Present for about one day, this image was taken at a distance, the patient also reports fatigue, located on the arm — 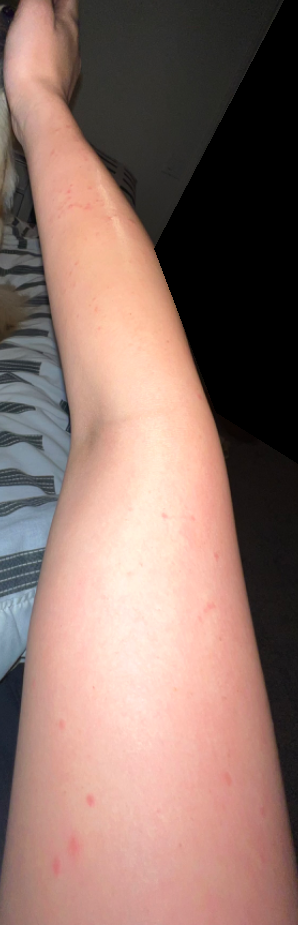Case summary:
- impression · Folliculitis (weight 0.54); Insect Bite (weight 0.23); Irritant Contact Dermatitis (weight 0.23)